A subject 62 years old. A smartphone photograph of a skin lesion:
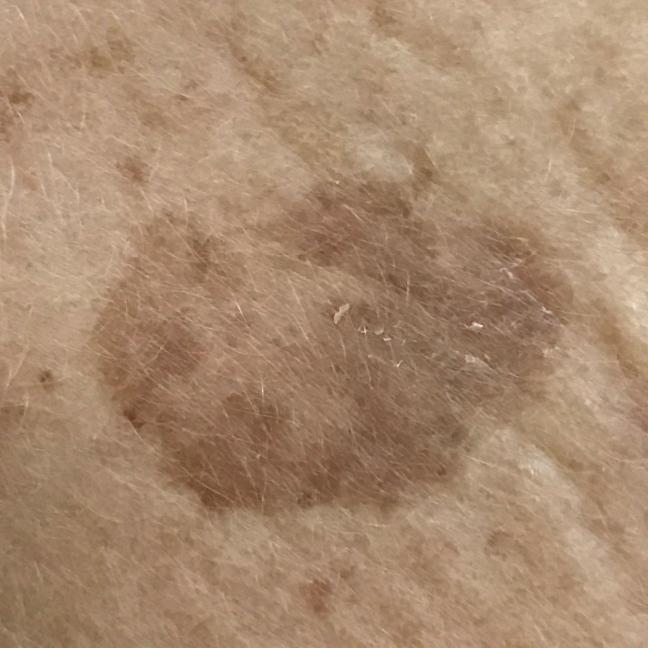Findings:
– body site: the face
– impression: seborrheic keratosis (clinical consensus)